A dermoscopic photograph of a skin lesion:
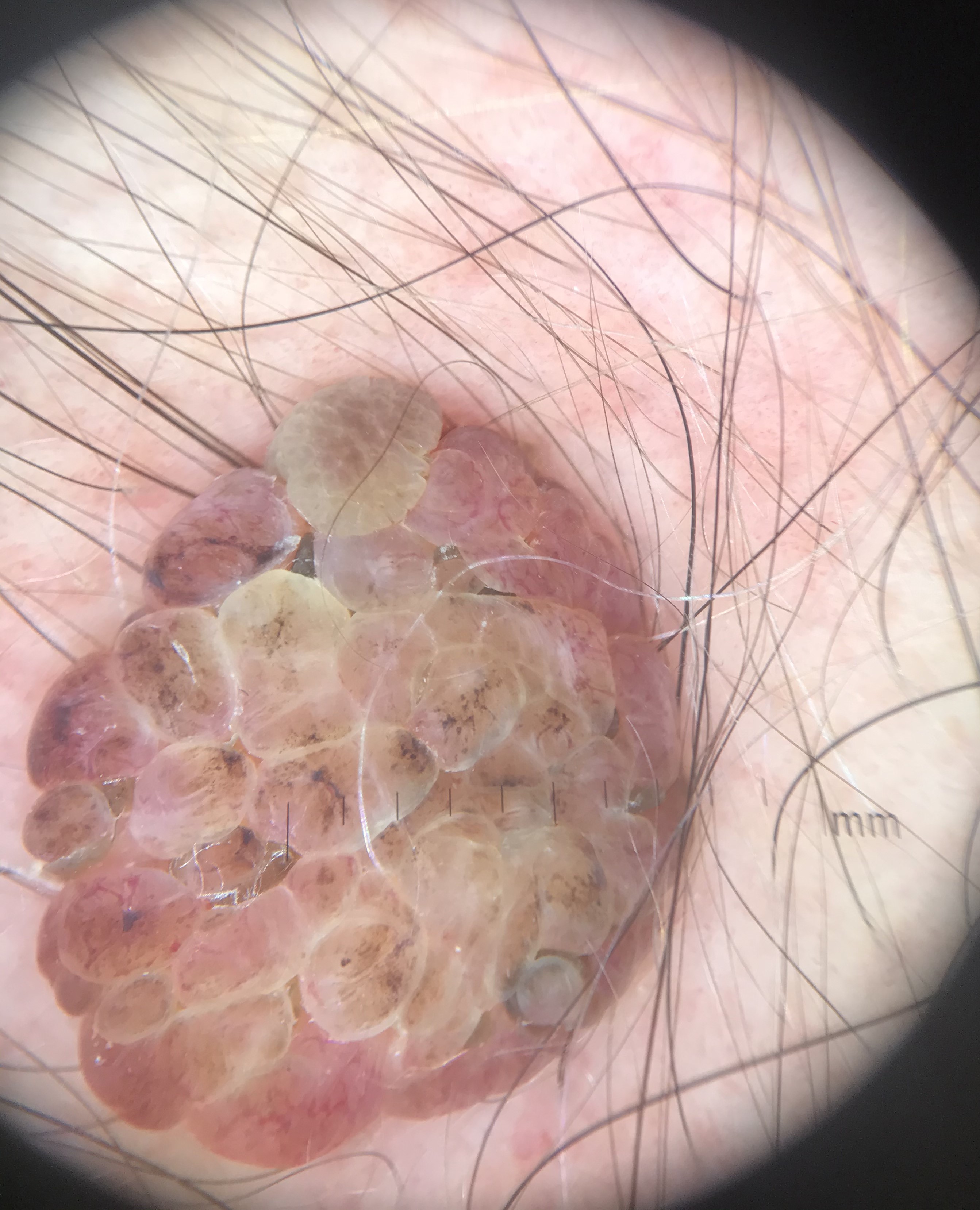Case:
- lesion type · banal
- assessment · dermal nevus (expert consensus)